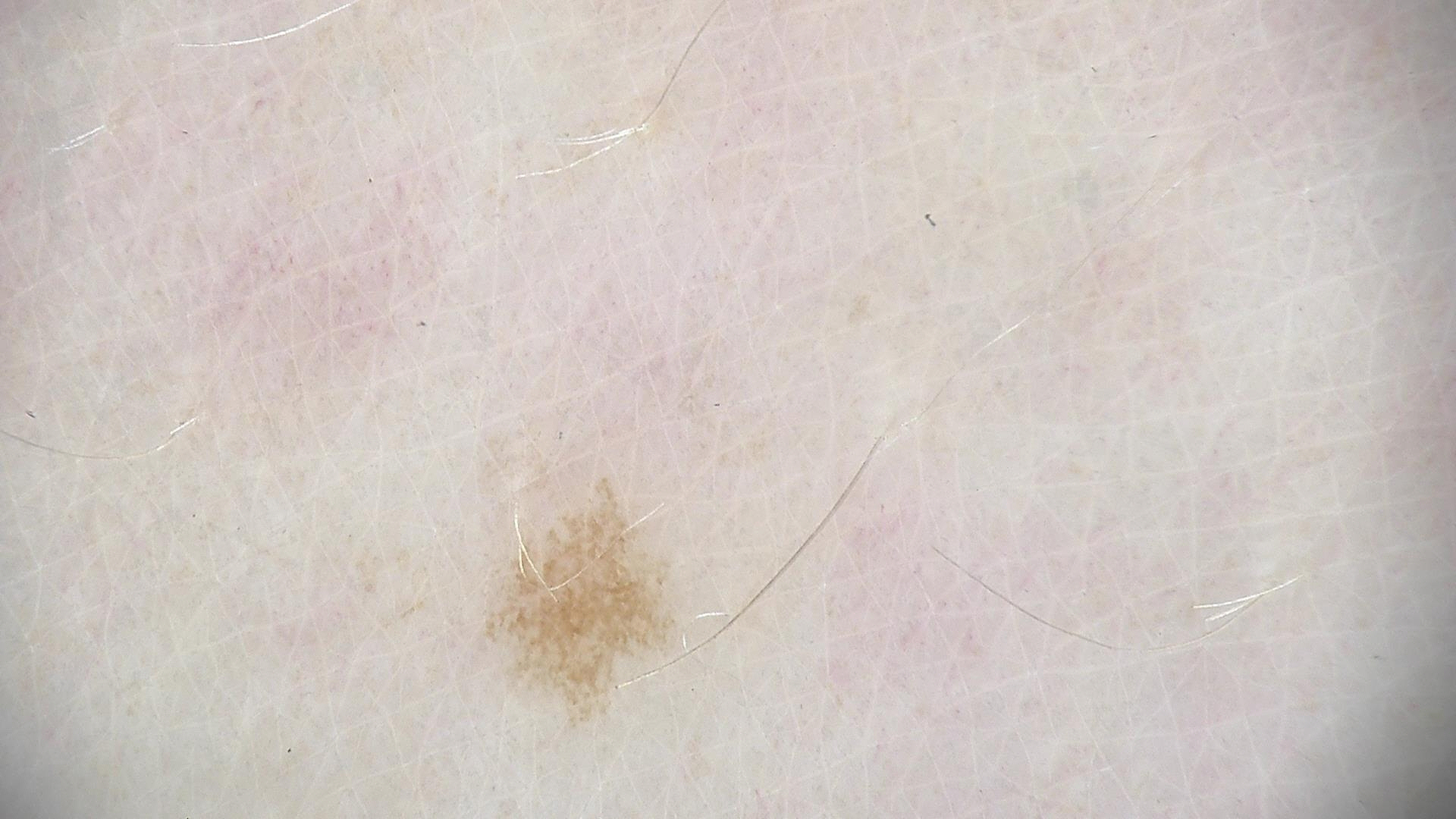image=dermoscopy
class=dysplastic junctional nevus (expert consensus)